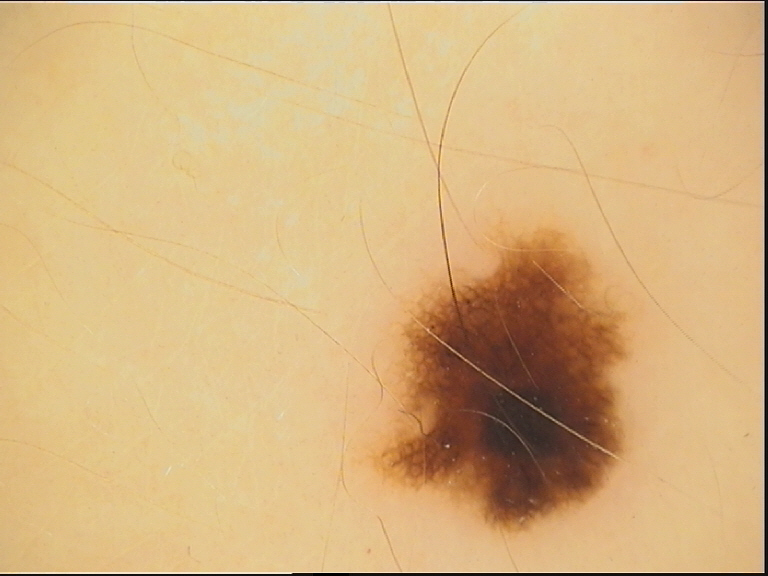A dermoscopic photograph of a skin lesion.
Classified as a dysplastic junctional nevus.